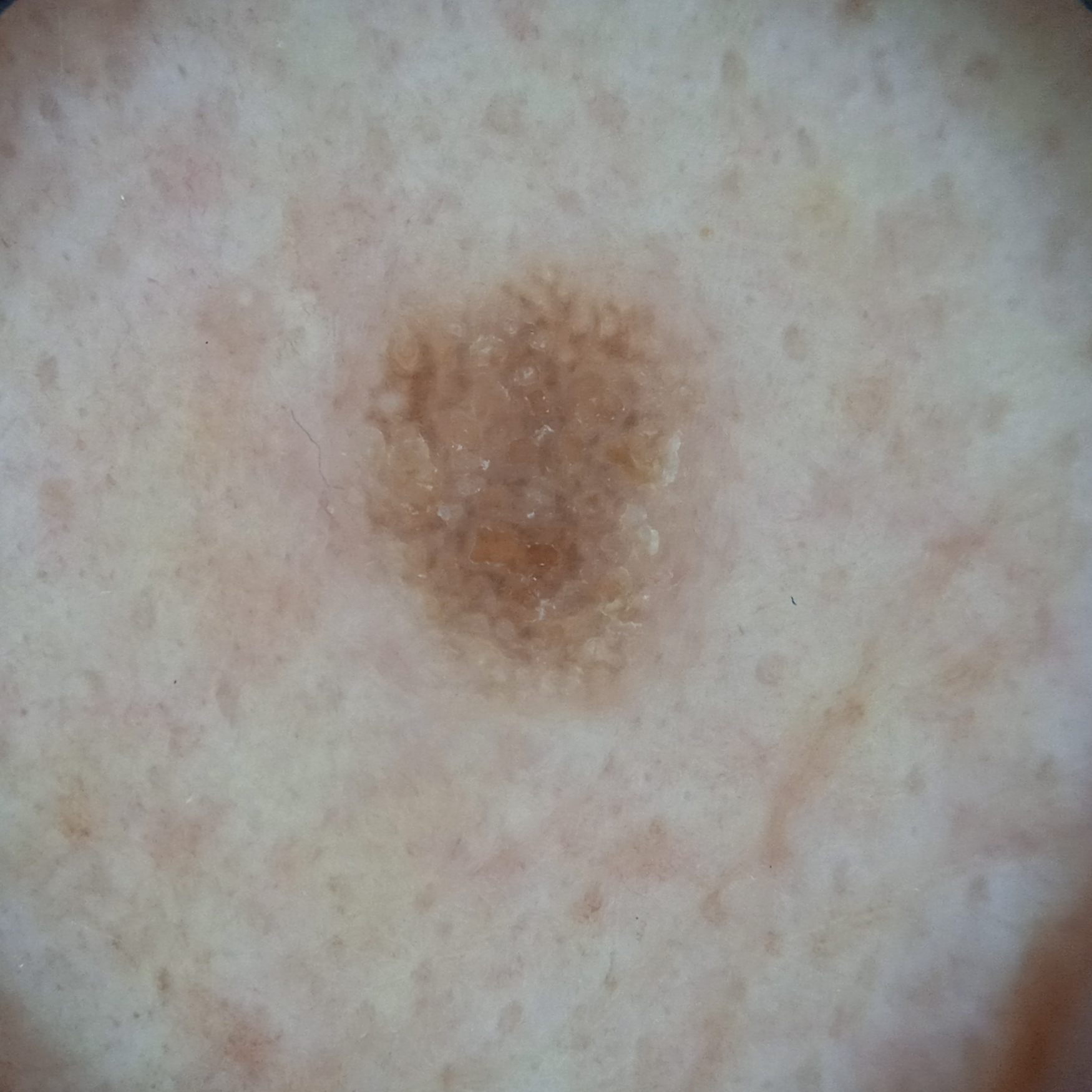| field | value |
|---|---|
| sun reaction | skin reddens painfully with sun exposure |
| subject | female, aged 81 |
| nevus count | a moderate number of melanocytic nevi |
| clinical context | research study (no referral diagnosis) |
| imaging | dermatoscopic image |
| site | the face |
| diameter | 5.3 mm |
| diagnostic label | seborrheic keratosis (dermatologist consensus) |